A dermoscopic image of a skin lesion.
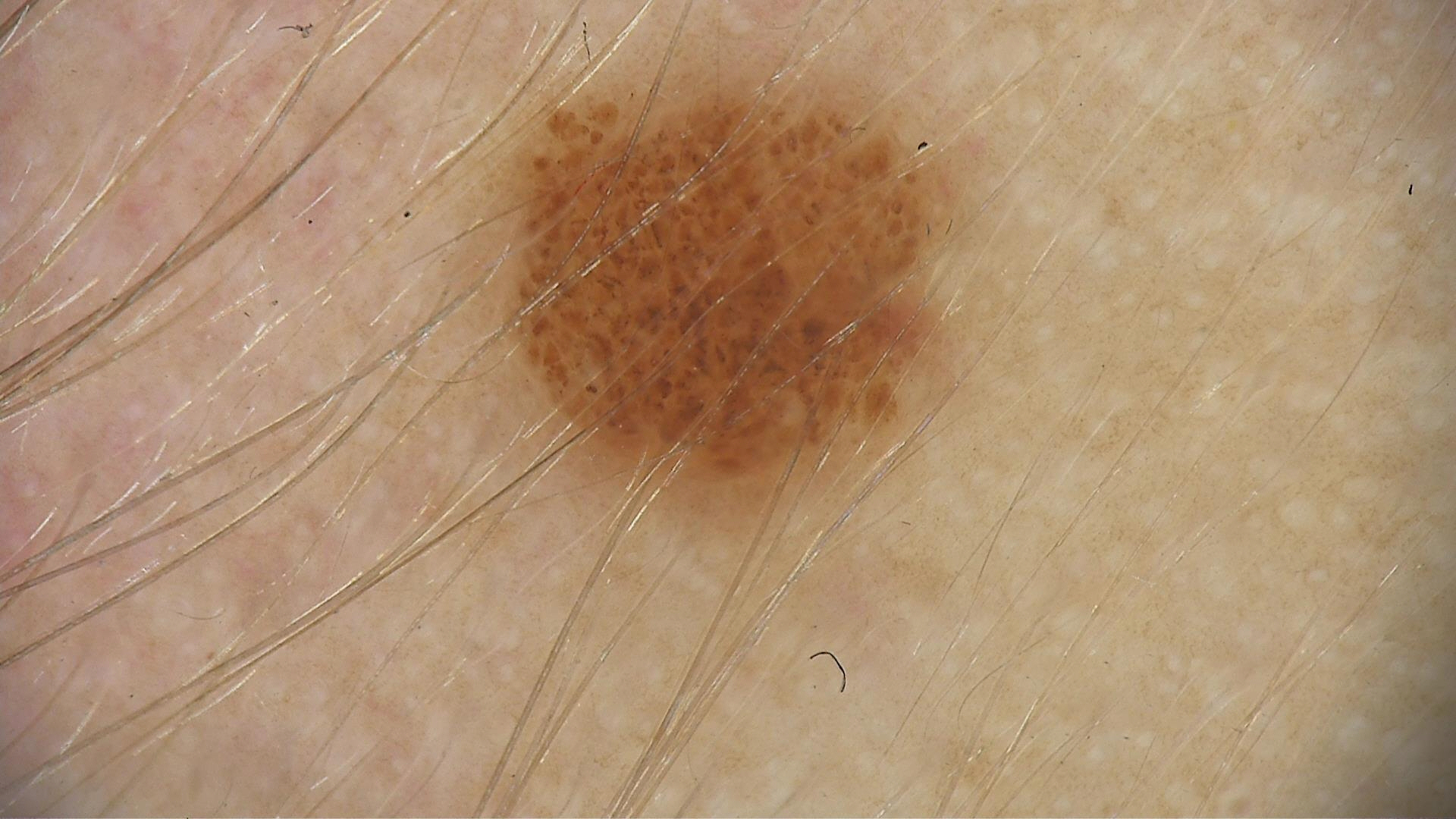Consistent with a dysplastic junctional nevus.